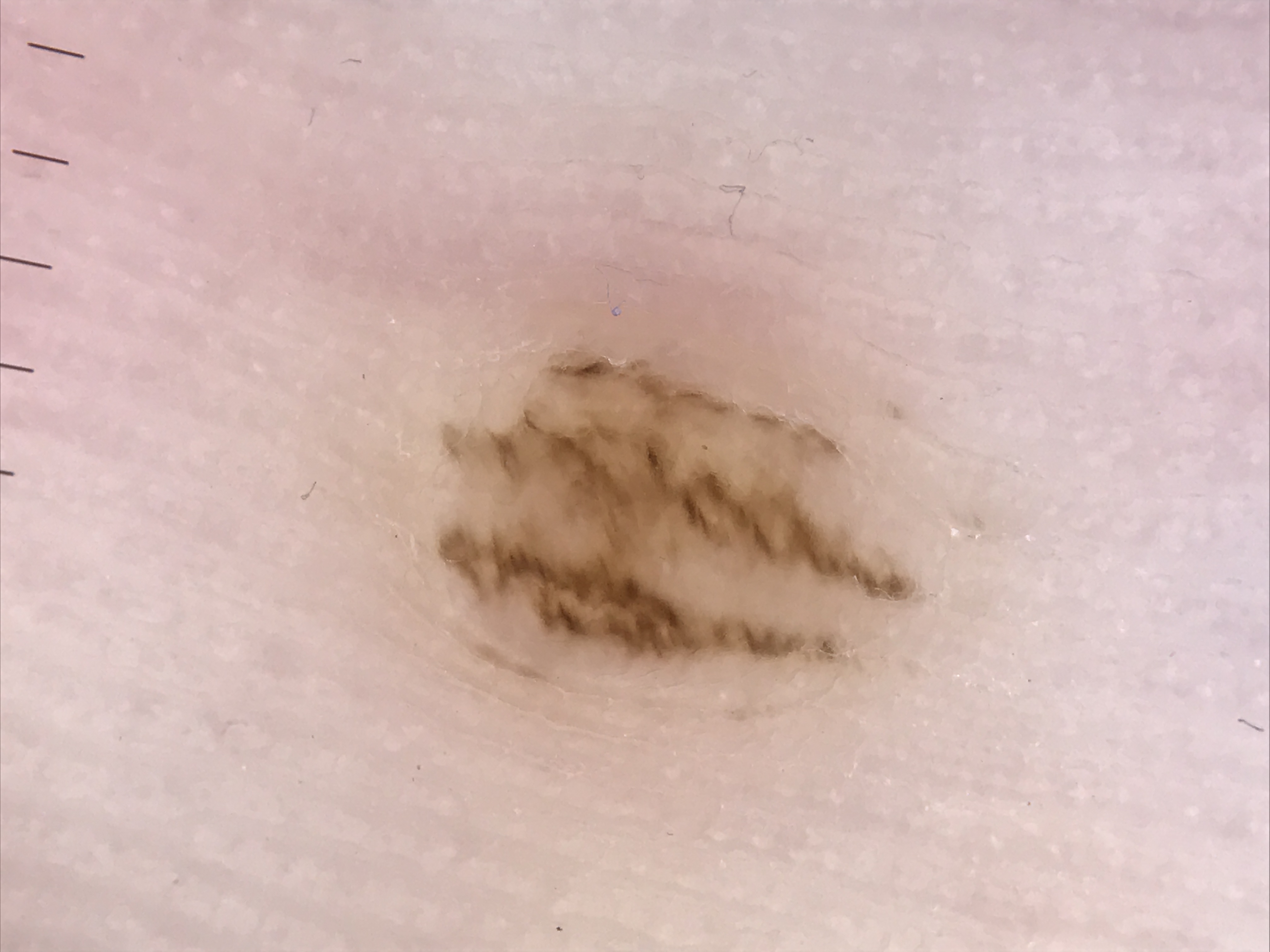Q: What was the diagnostic impression?
A: acral compound nevus (expert consensus)